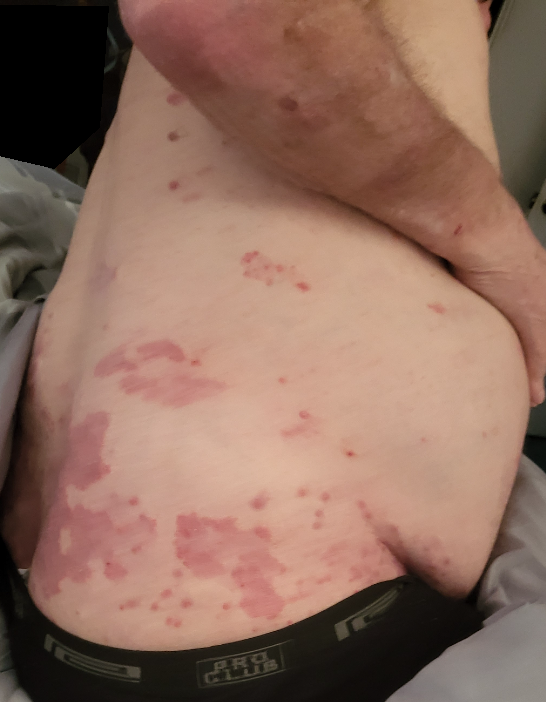Assessment: The case was indeterminate on photographic review. Clinical context: The photograph was taken at a distance.